A dermoscopic image of a skin lesion: 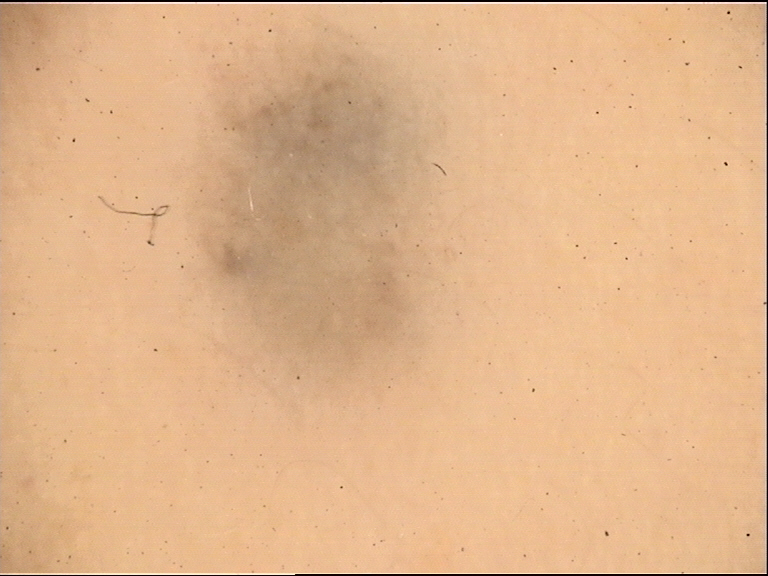Findings:
• category · banal, dermal
• assessment · blue nevus (expert consensus)